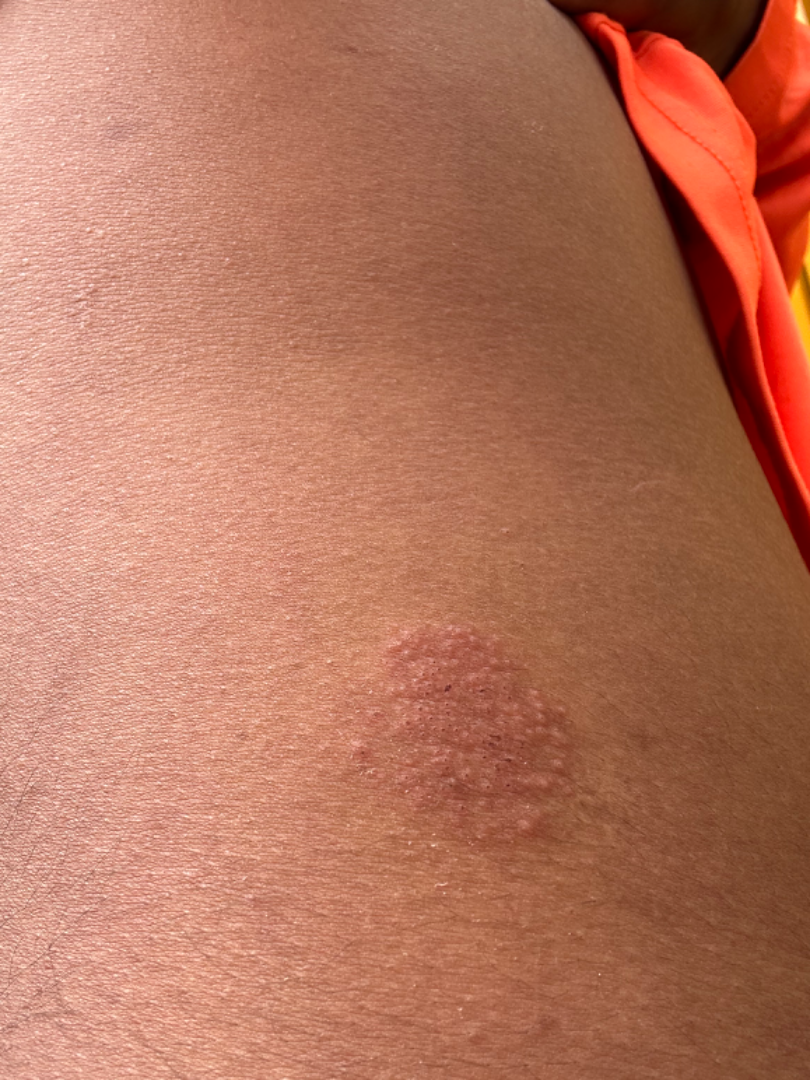No differential diagnosis could be assigned on photographic review.